A clinical close-up photograph of a skin lesion; a patient 59 years of age:
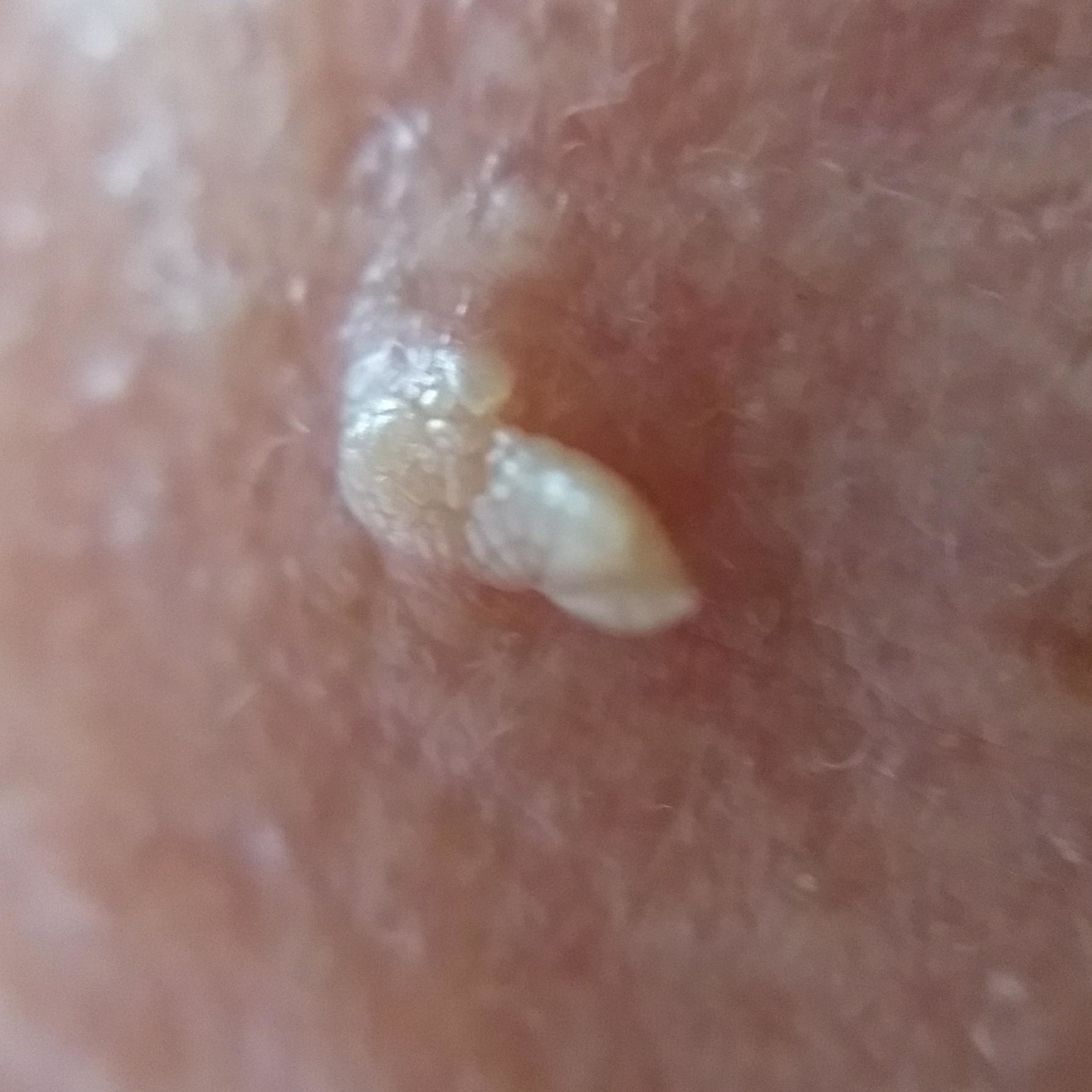The lesion is located on the face. The patient reports that the lesion is elevated. Consistent with an actinic keratosis.